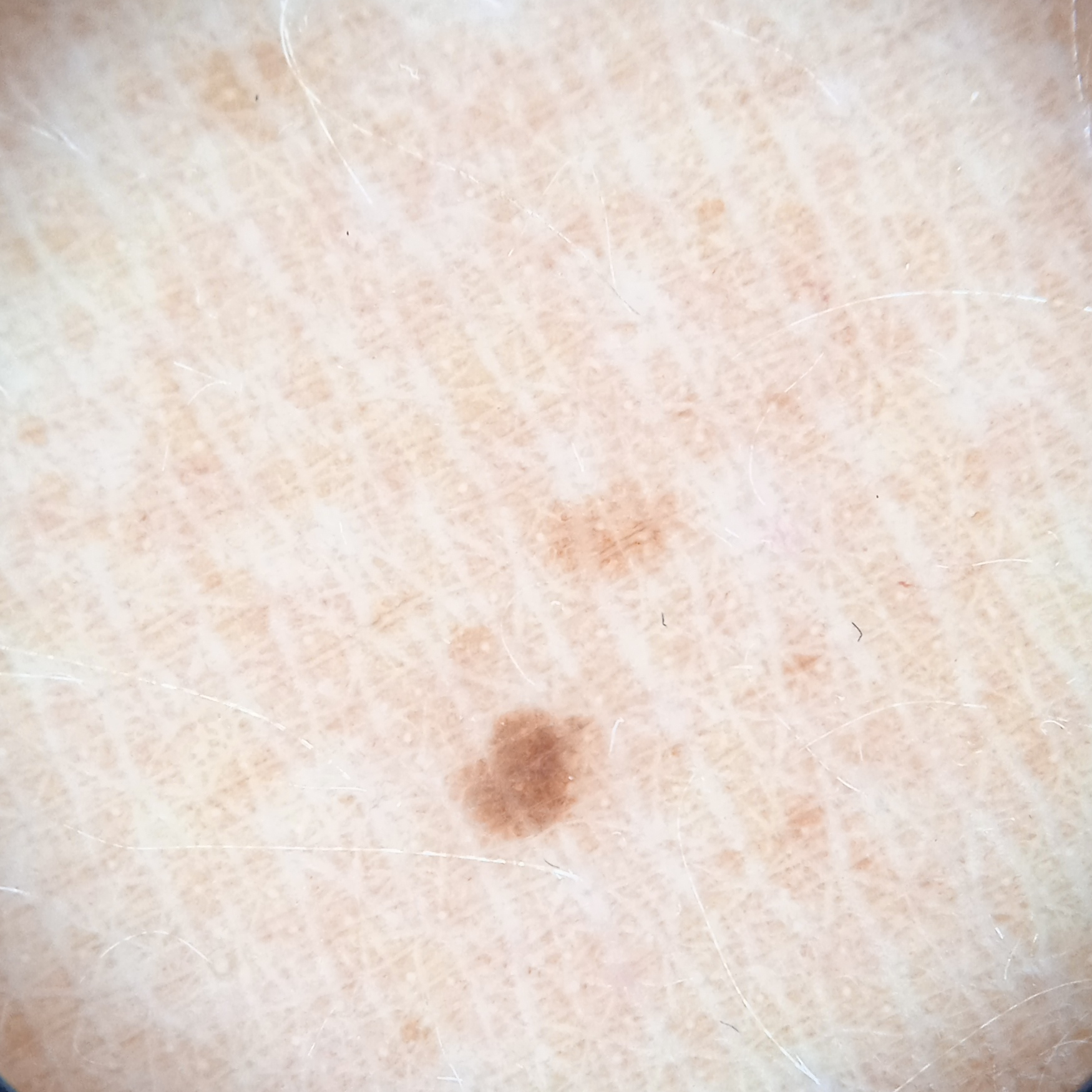By self-report, a history of sunbed use. A female subject age 47. A dermatoscopic image of a skin lesion. The patient says their skin tans without first burning. Acquired for a research image collection, with no referral diagnosis. The patient describes having a moderate number of moles. The lesion is located on the back. The lesion measures approximately 1.8 mm. The lesion was assessed as a melanocytic nevus.